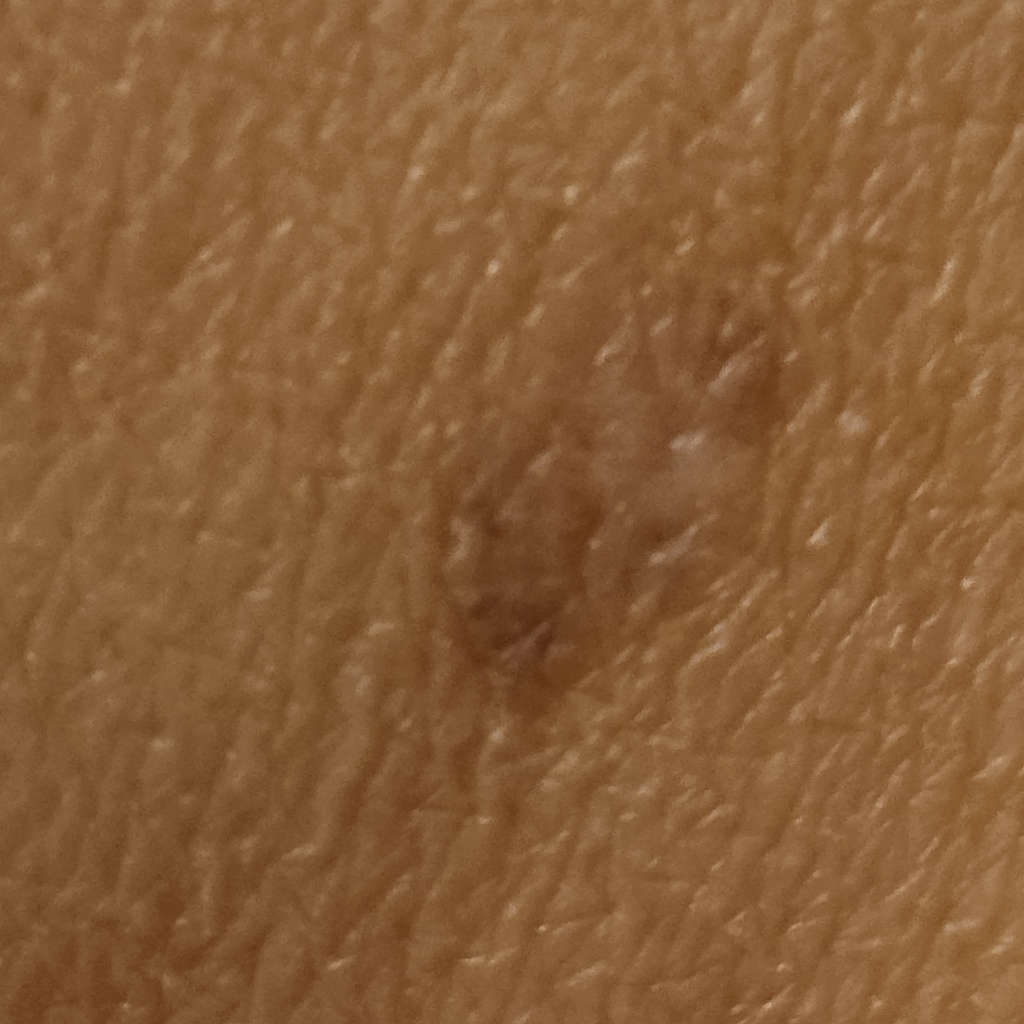Dermatologist review favored a melanocytic nevus.